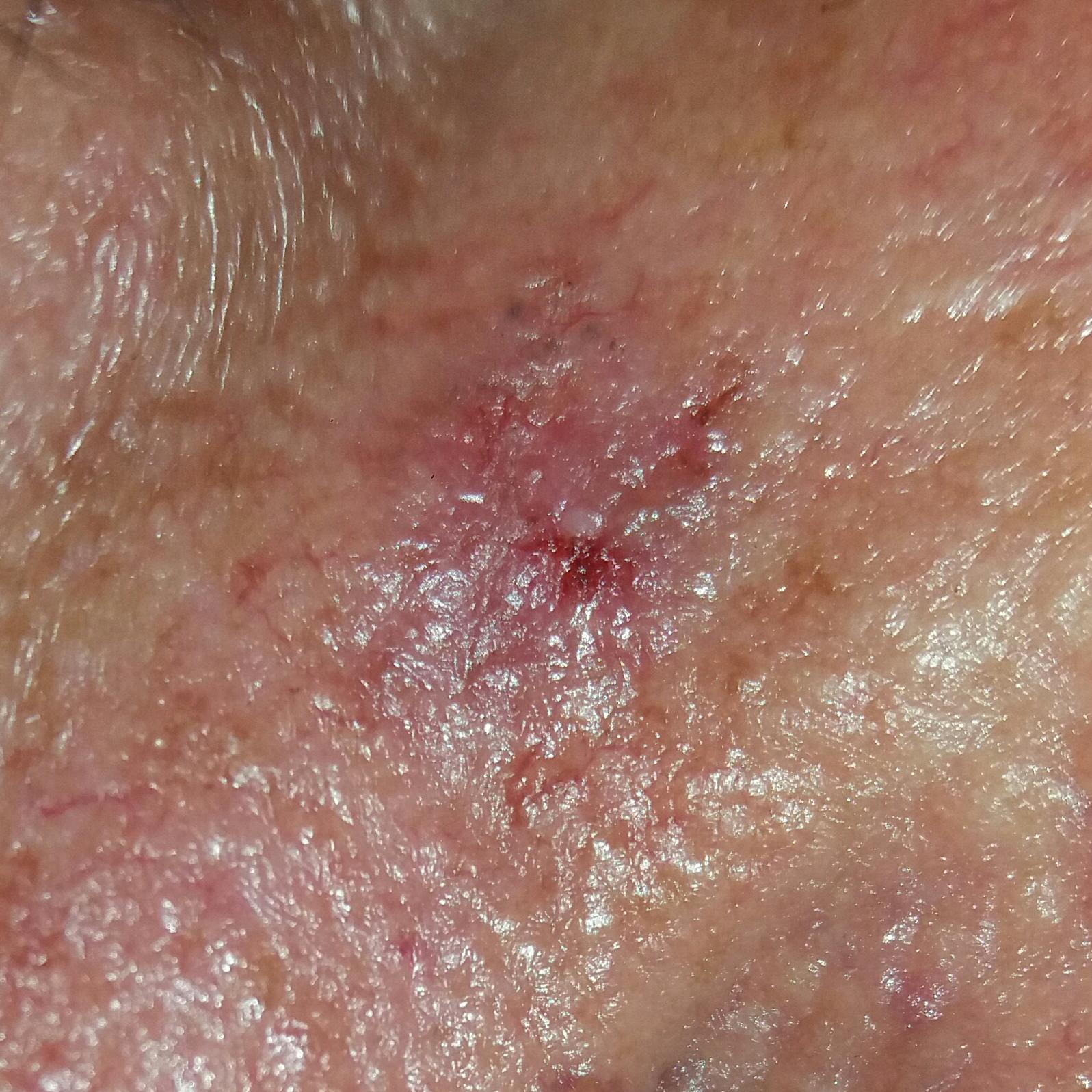A clinical close-up photograph of a skin lesion. History notes alcohol use and prior skin cancer (patient or family). The patient is Fitzpatrick phototype IV. Histopathological examination showed a basal cell carcinoma.